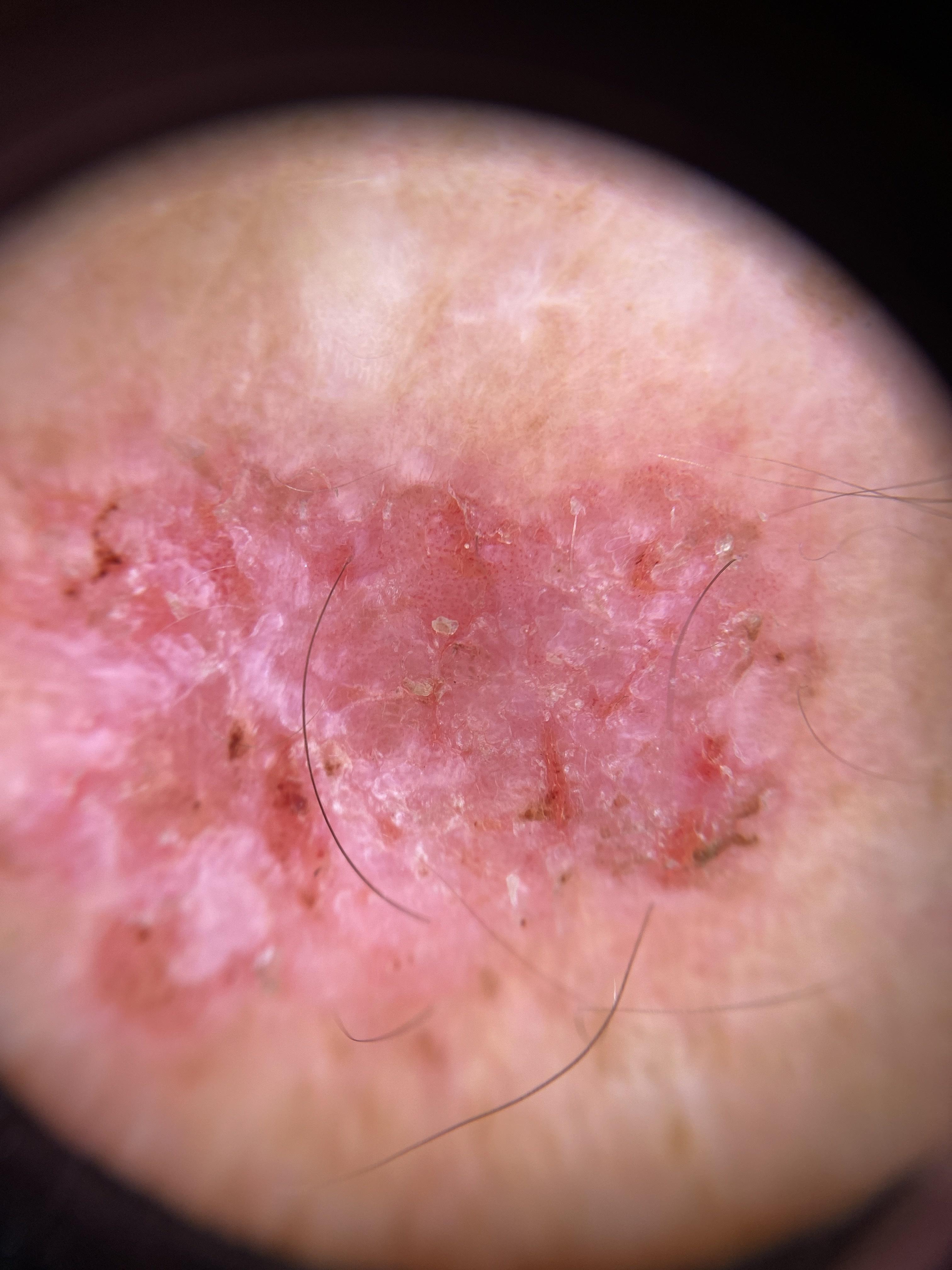A contact-polarized dermoscopy image of a skin lesion. A male patient aged approximately 65. The lesion was found on an upper extremity. Histopathologically confirmed as a squamous cell carcinoma.